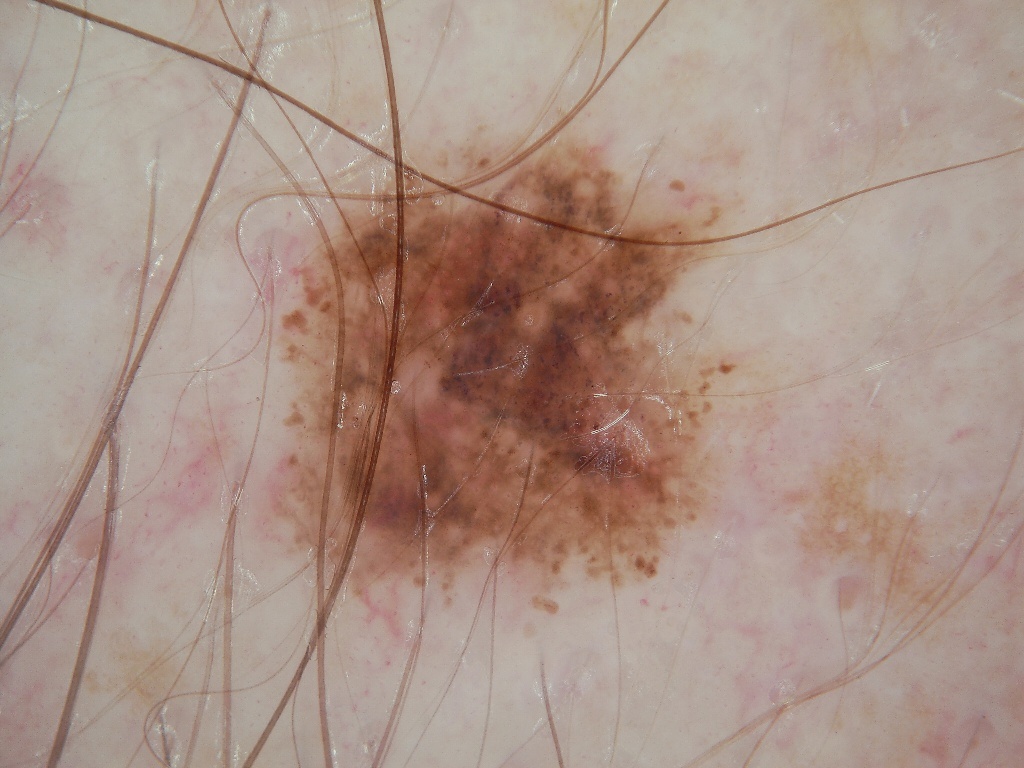Case summary:
The patient is a male aged 58 to 62. A dermatoscopic image of a skin lesion. A moderately sized lesion. The visible lesion spans box(270, 126, 770, 644). On dermoscopy, the lesion shows globules; no streaks, pigment network, negative network, or milia-like cysts.
Assessment:
Diagnosed as a melanocytic nevus, a benign lesion.